The condition has been present for three to twelve months; symptoms reported: bothersome appearance; texture is reported as rough or flaky; the photograph was taken at an angle; the arm is involved.
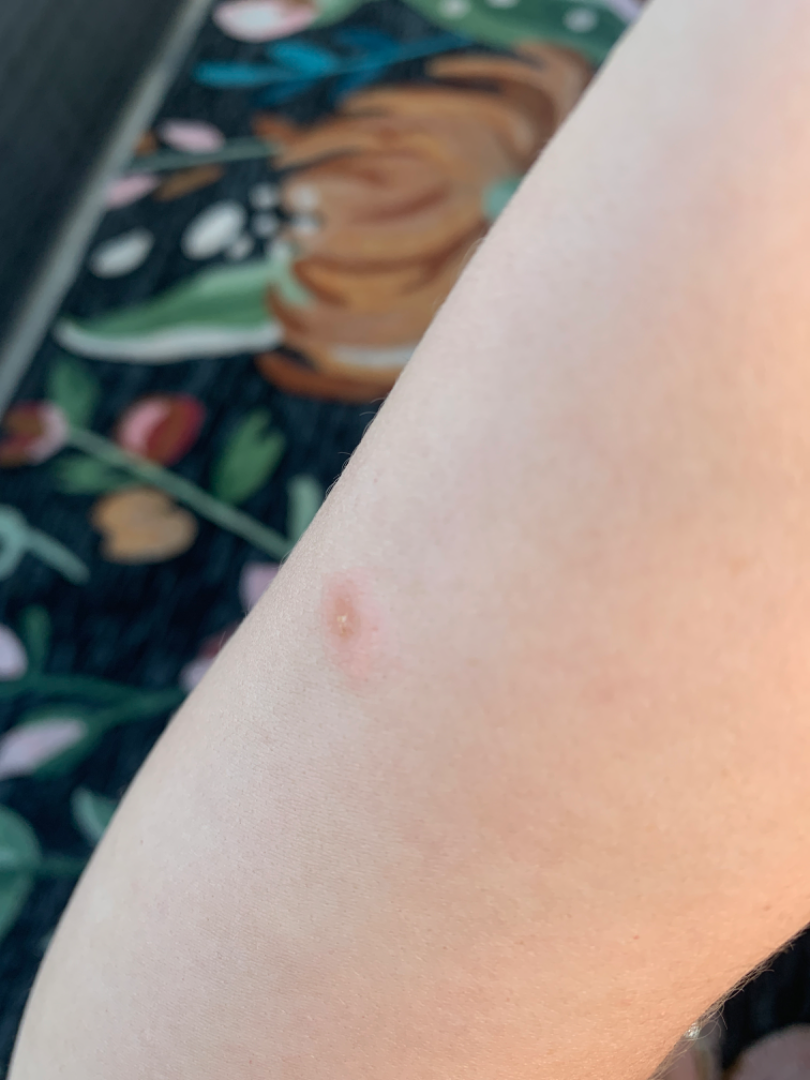Assessment:
The reviewer was unable to grade this case for skin condition.